A skin lesion imaged with a dermatoscope.
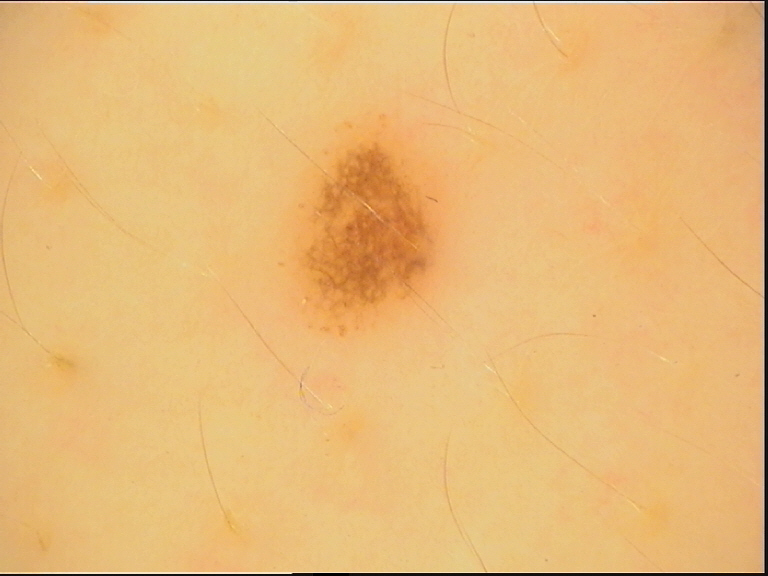Findings:
- label: dysplastic junctional nevus (expert consensus)